The photograph is a close-up of the affected area; skin tone: non-clinician graders estimated Monk Skin Tone 1 (US pool) or 3 (India pool):
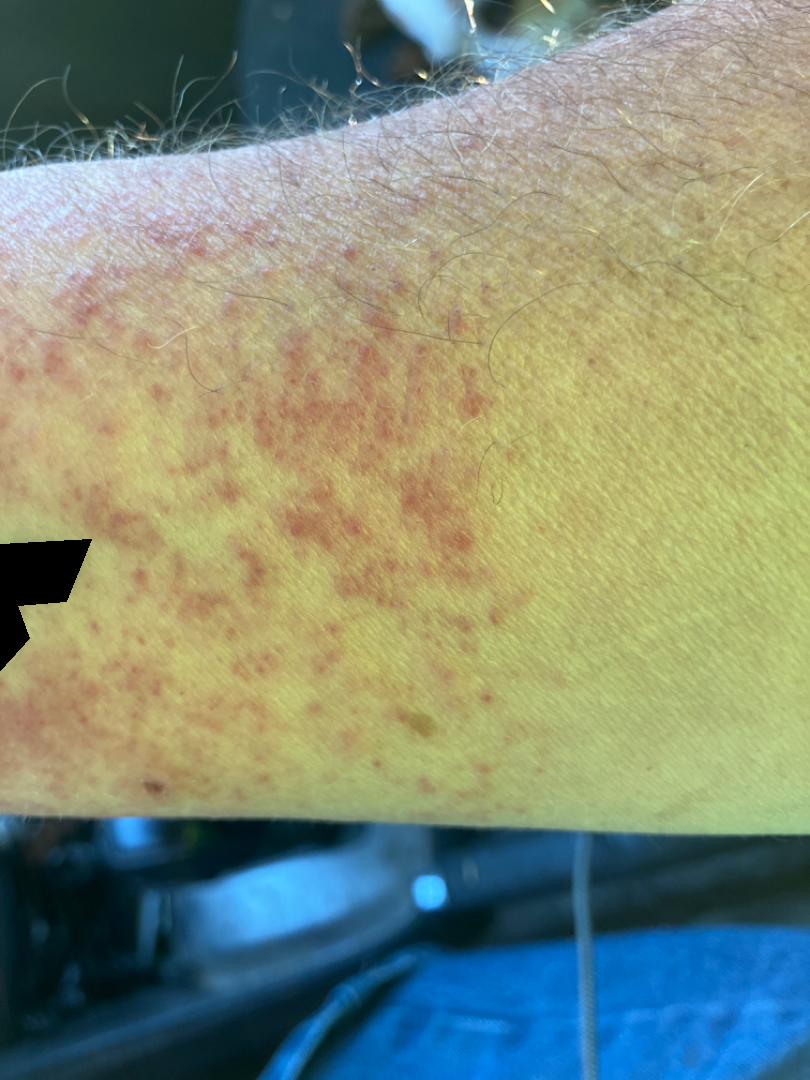Q: What was the assessment?
A: indeterminate from the photograph